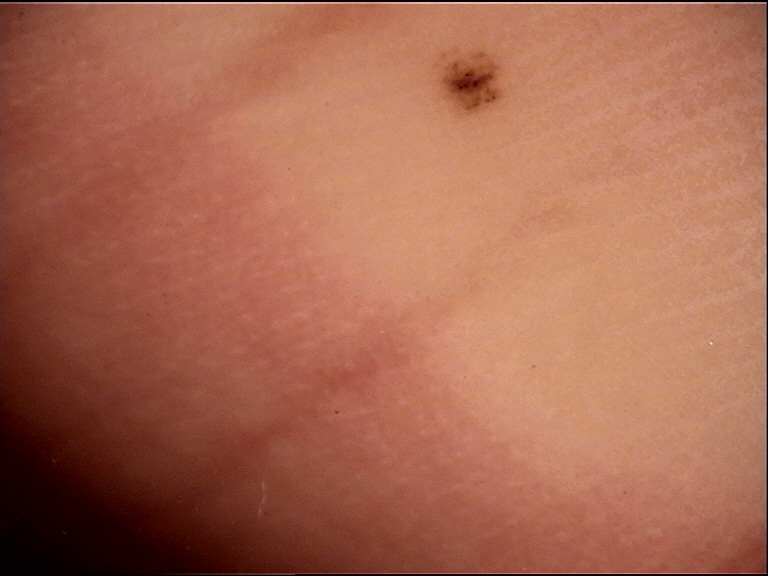Dermoscopy of a skin lesion.
The morphology is that of a banal lesion.
Diagnosed as an acral junctional nevus.